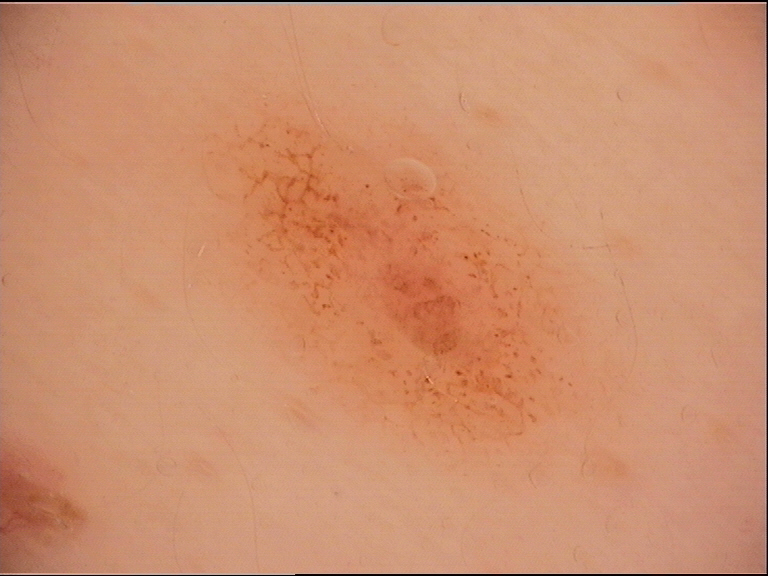The diagnostic label was a benign lesion — a dysplastic junctional nevus.